A smartphone photograph of a skin lesion:
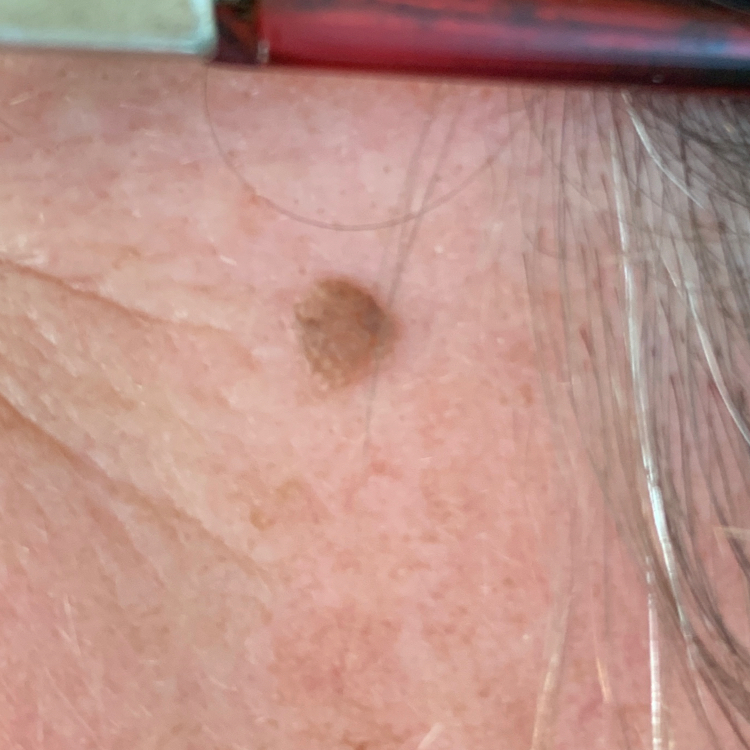Findings: The lesion is on the face. Per patient report, the lesion is elevated, but does not hurt and does not itch. Conclusion: The consensus clinical diagnosis was a seborrheic keratosis.